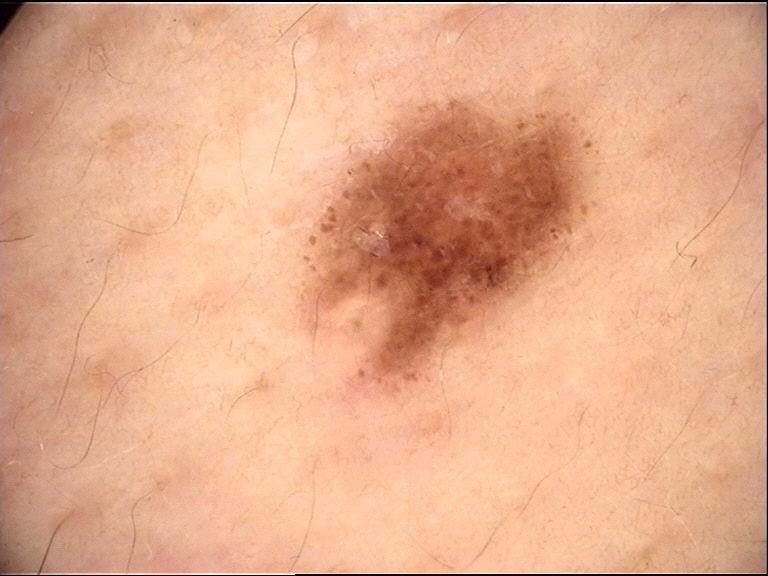modality = dermatoscopy | class = dysplastic junctional nevus (expert consensus).